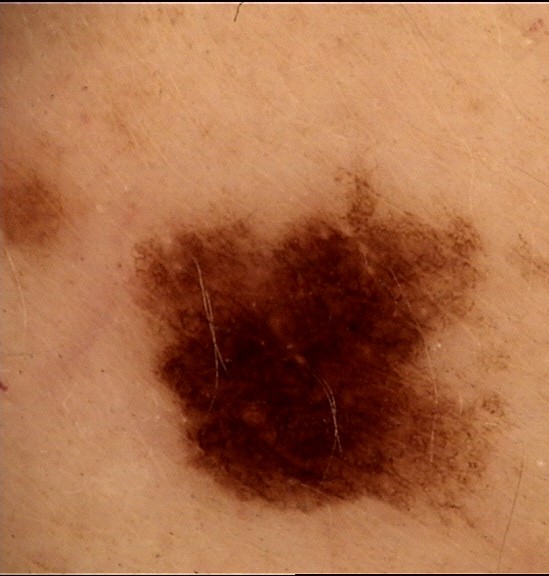{
  "diagnosis": {
    "name": "dysplastic junctional nevus",
    "code": "jd",
    "malignancy": "benign",
    "super_class": "melanocytic",
    "confirmation": "expert consensus"
  }
}